Reported lesion symptoms include itching; the patient reported no systemic symptoms; the photo was captured at an angle; the condition has been present for about one day; the affected area is the arm; the patient indicates the lesion is raised or bumpy; self-categorized by the patient as a rash; the subject is male: 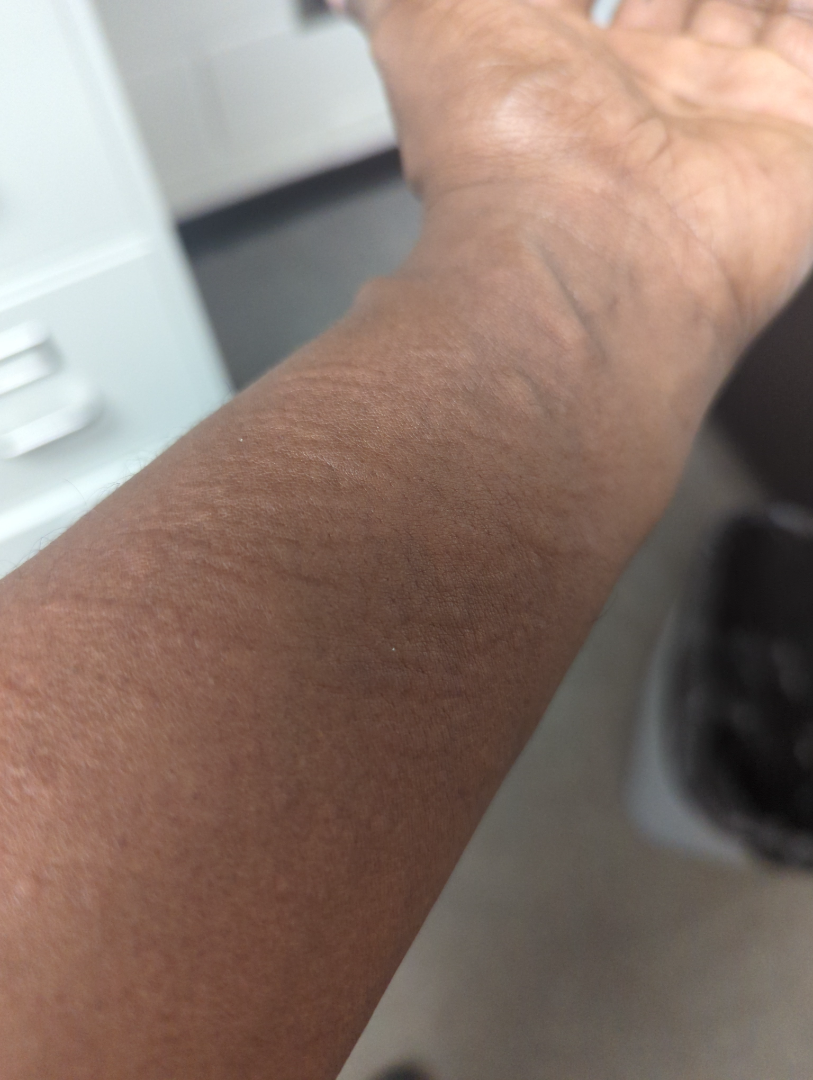Q: What conditions are considered?
A: the leading impression is Urticaria; a remote consideration is Flagellate erythema; less likely is Leukocytoclastic Vasculitis